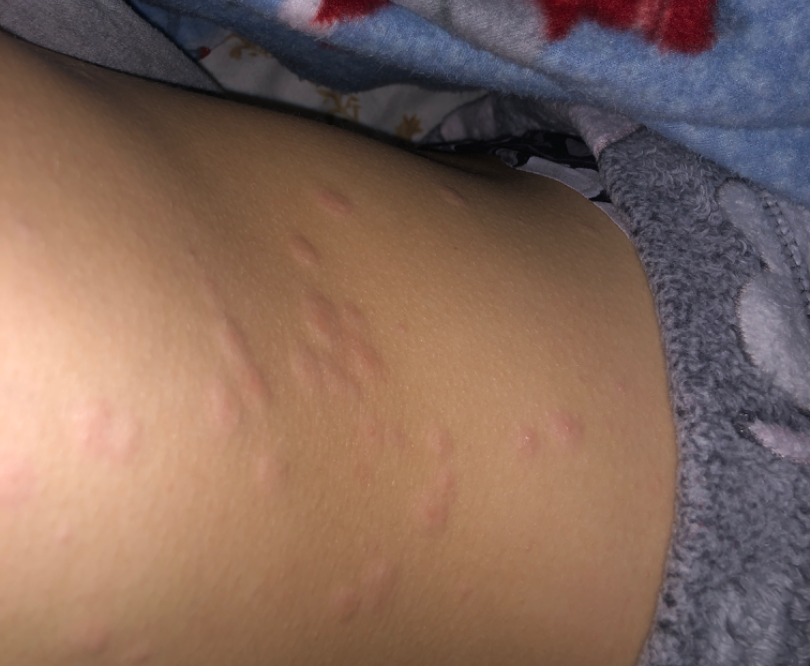{
  "differential": {
    "leading": [
      "Urticaria"
    ]
  }
}